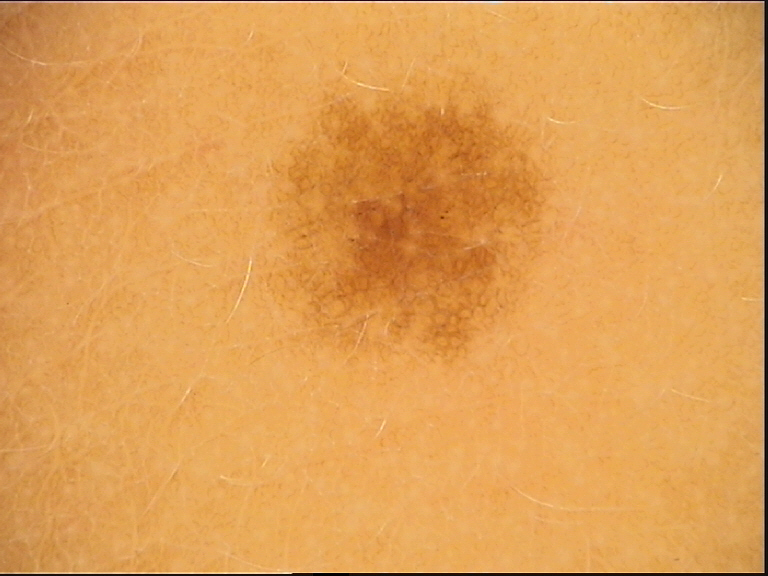Findings: A dermoscopic photograph of a skin lesion. Conclusion: The diagnosis was a banal lesion — a junctional nevus.